The contributor notes the condition has been present for about one day, this image was taken at an angle, Fitzpatrick phototype III; lay graders estimated MST 2 or 5, the leg and top or side of the foot are involved, the lesion is described as raised or bumpy.
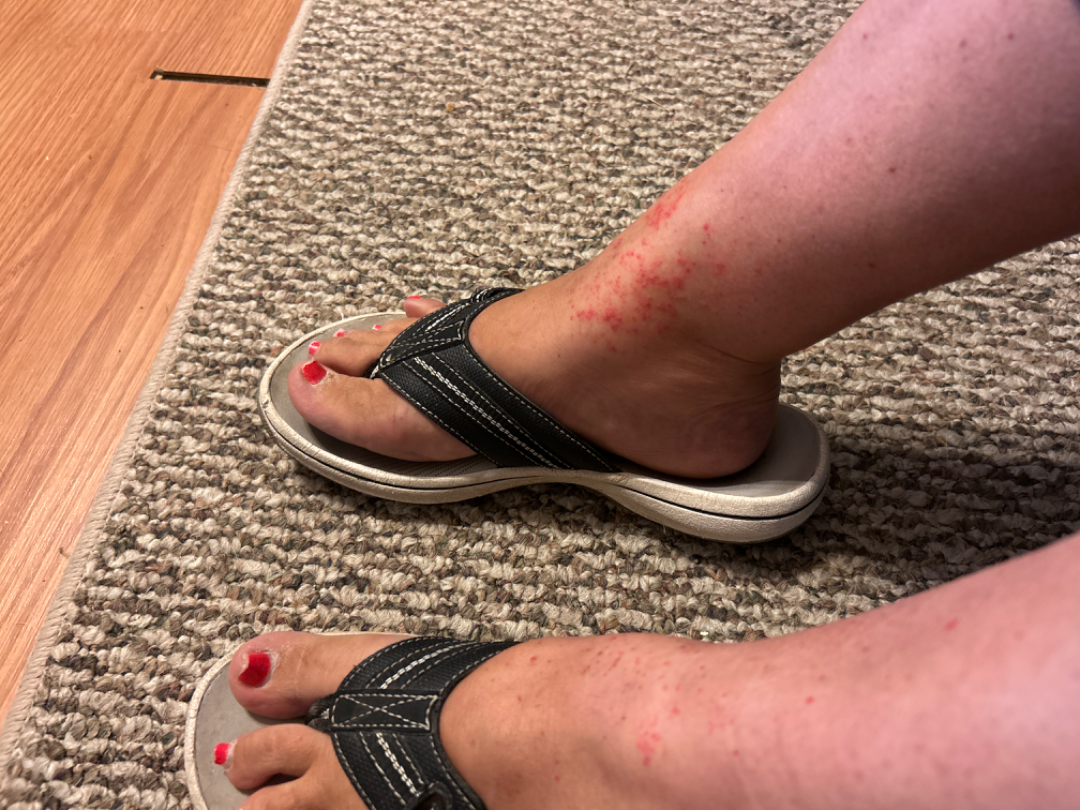Pigmented purpuric eruption (leading); Purpura (possible); Vasculitis of the skin (possible).